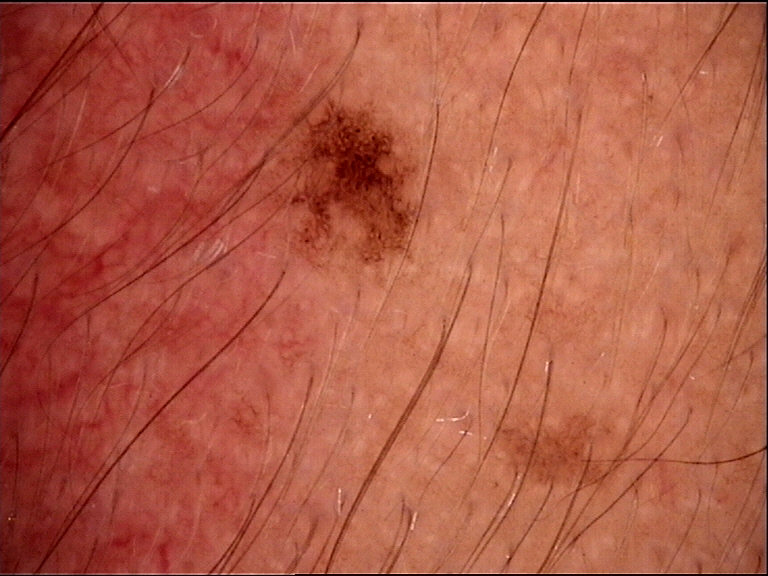Classified as a junctional nevus.